A close-up photograph. Self-categorized by the patient as a rash. Skin tone: FST III. The patient notes the lesion is rough or flaky. The patient is female. The lesion is associated with bothersome appearance: 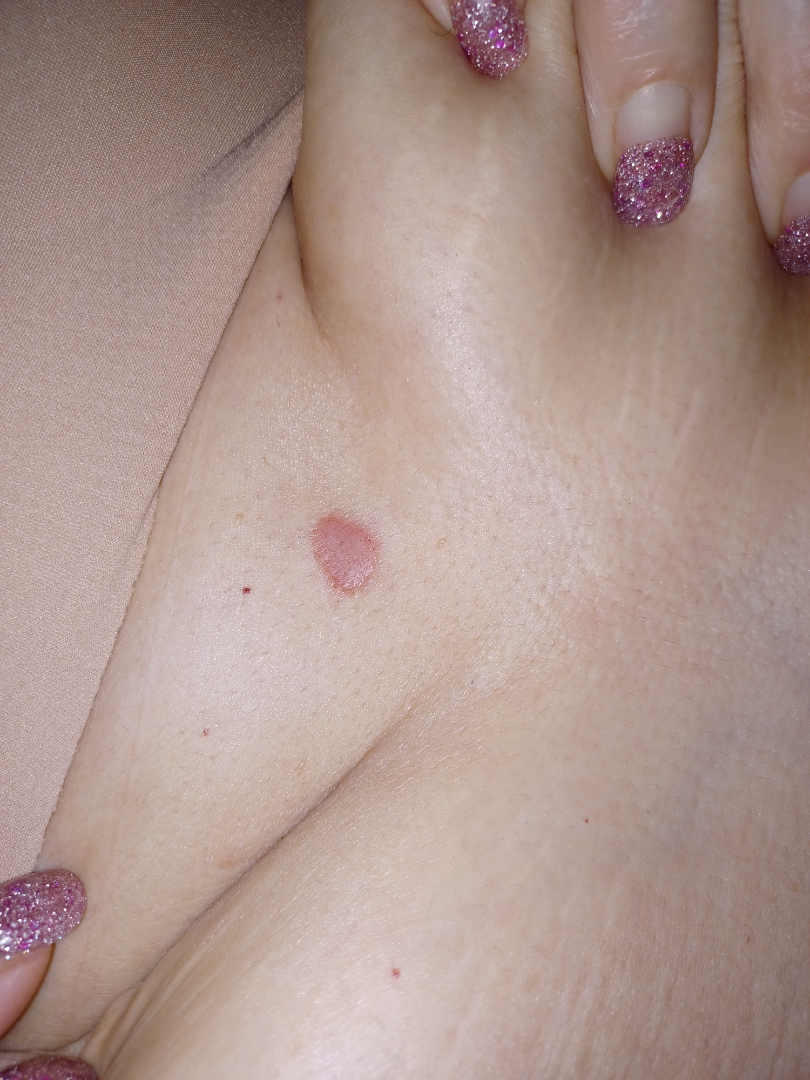Notes:
* differential · Scar Condition (favored); Basal Cell Carcinoma (considered)